A male subject, approximately 60 years of age; this is a dermoscopic photograph of a skin lesion — 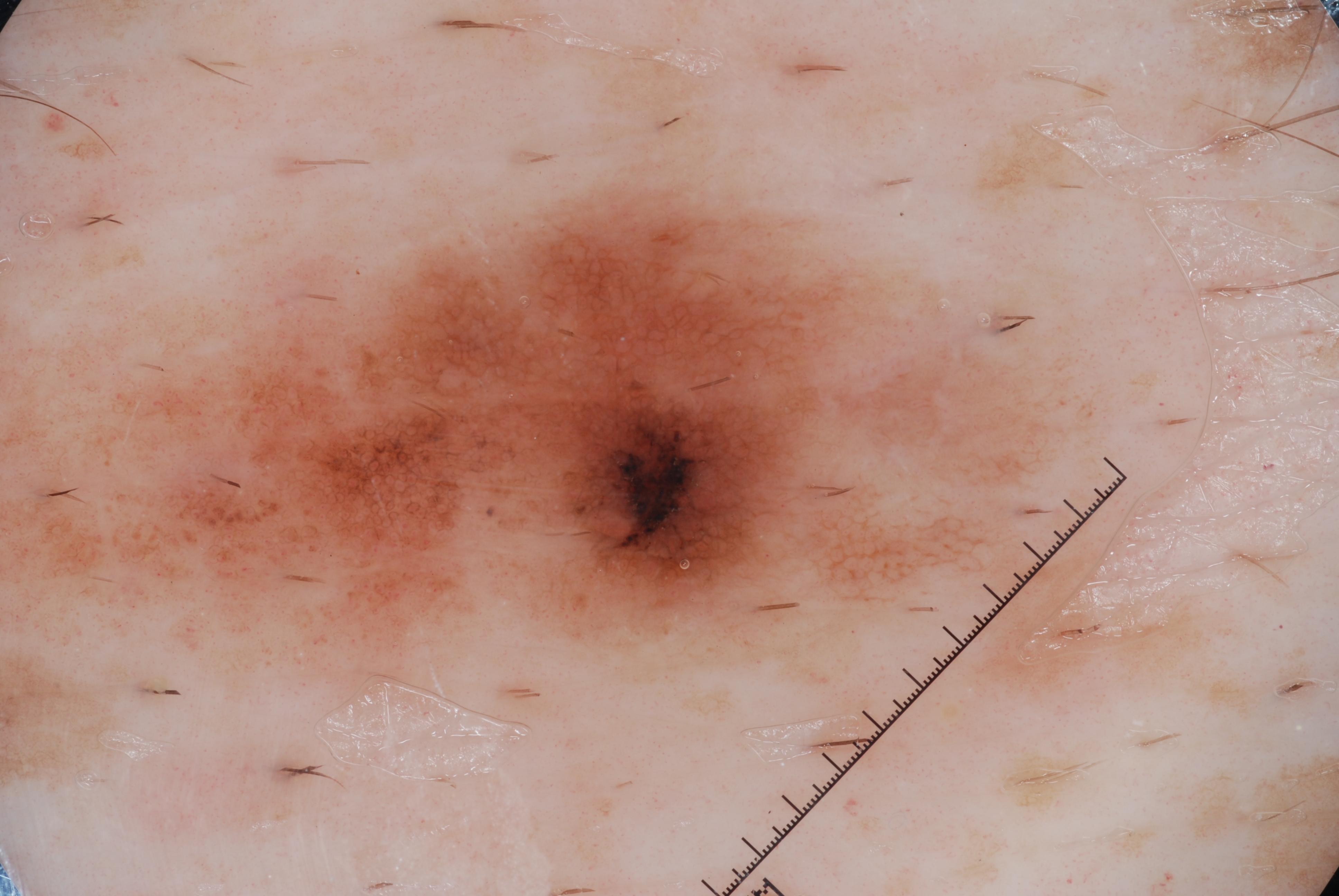Q: Where is the lesion in the image?
A: left=1, top=183, right=1073, bottom=790
Q: Which dermoscopic features were noted?
A: pigment network and milia-like cysts; absent: negative network and streaks
Q: What did the assessment conclude?
A: a melanocytic nevus